Dermoscopy of a skin lesion.
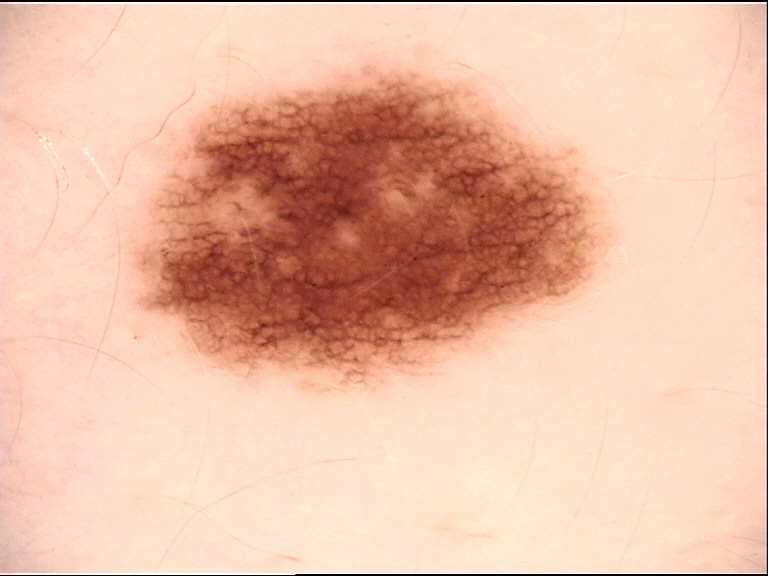The diagnosis was a dysplastic junctional nevus.